A dermatoscopic image of a skin lesion.
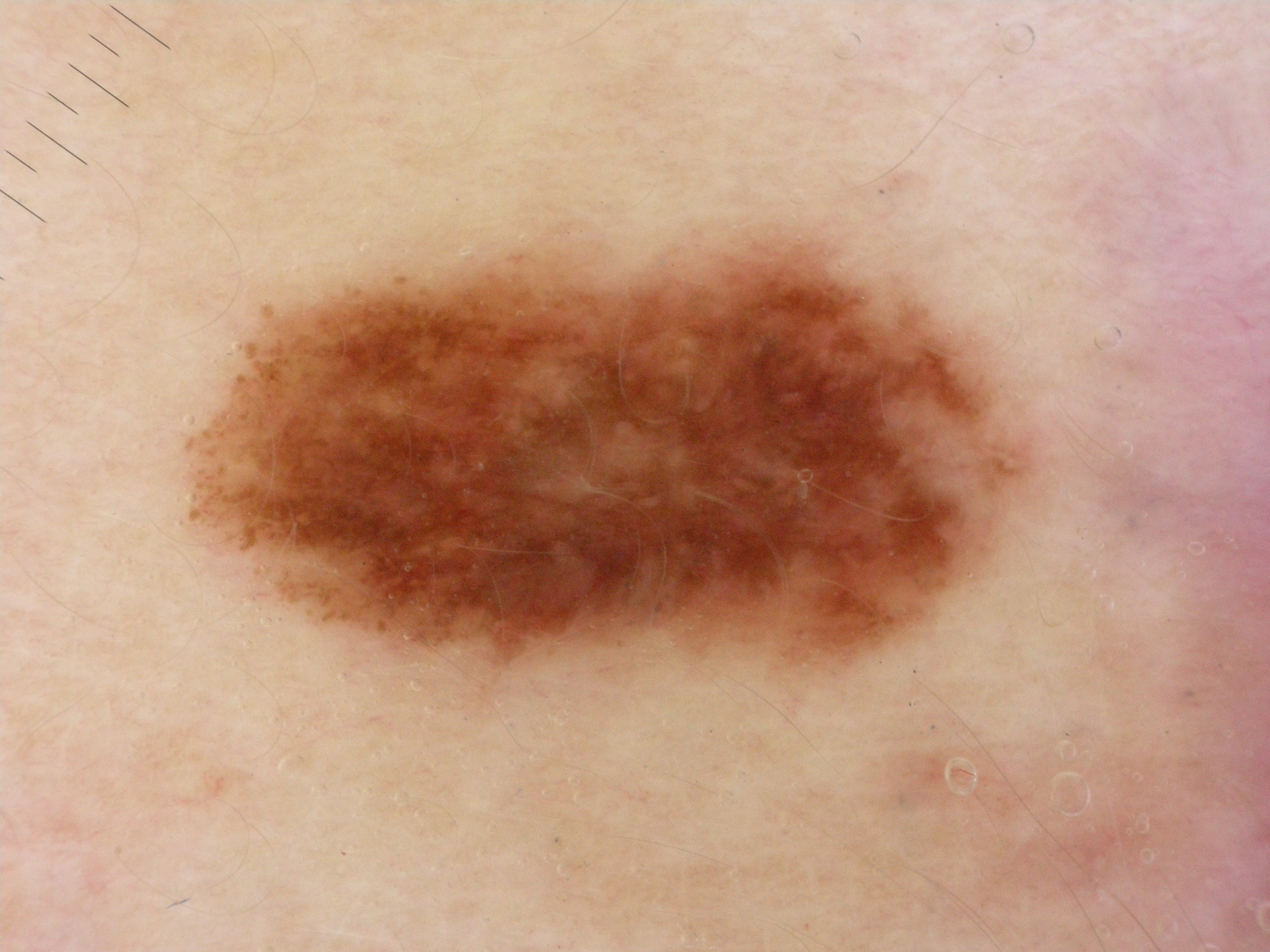Findings:
The lesion covers approximately 23% of the dermoscopic field. With coordinates (x1, y1, x2, y2), lesion location: bbox(192, 238, 1037, 693). Dermoscopic assessment notes globules and pigment network.
Conclusion:
Expert review diagnosed this as a melanocytic nevus.